Female patient, age 30–39 · an image taken at a distance · the leg is involved:
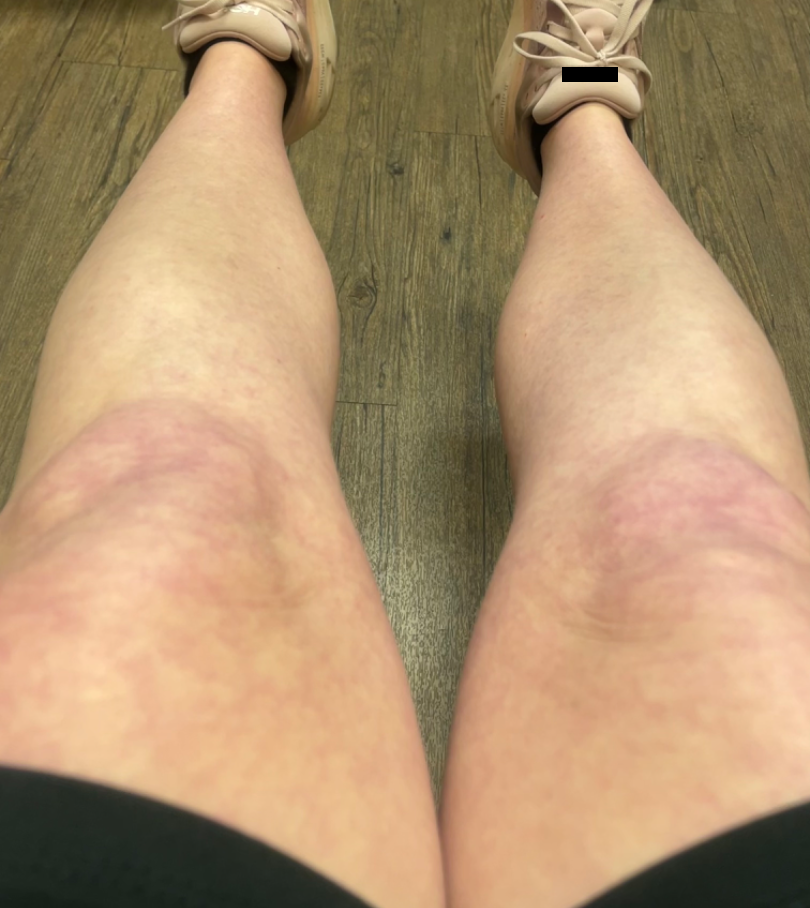Reviewed remotely by three dermatologists: most likely Livedo reticularis; also on the differential is Erythema ab igne.